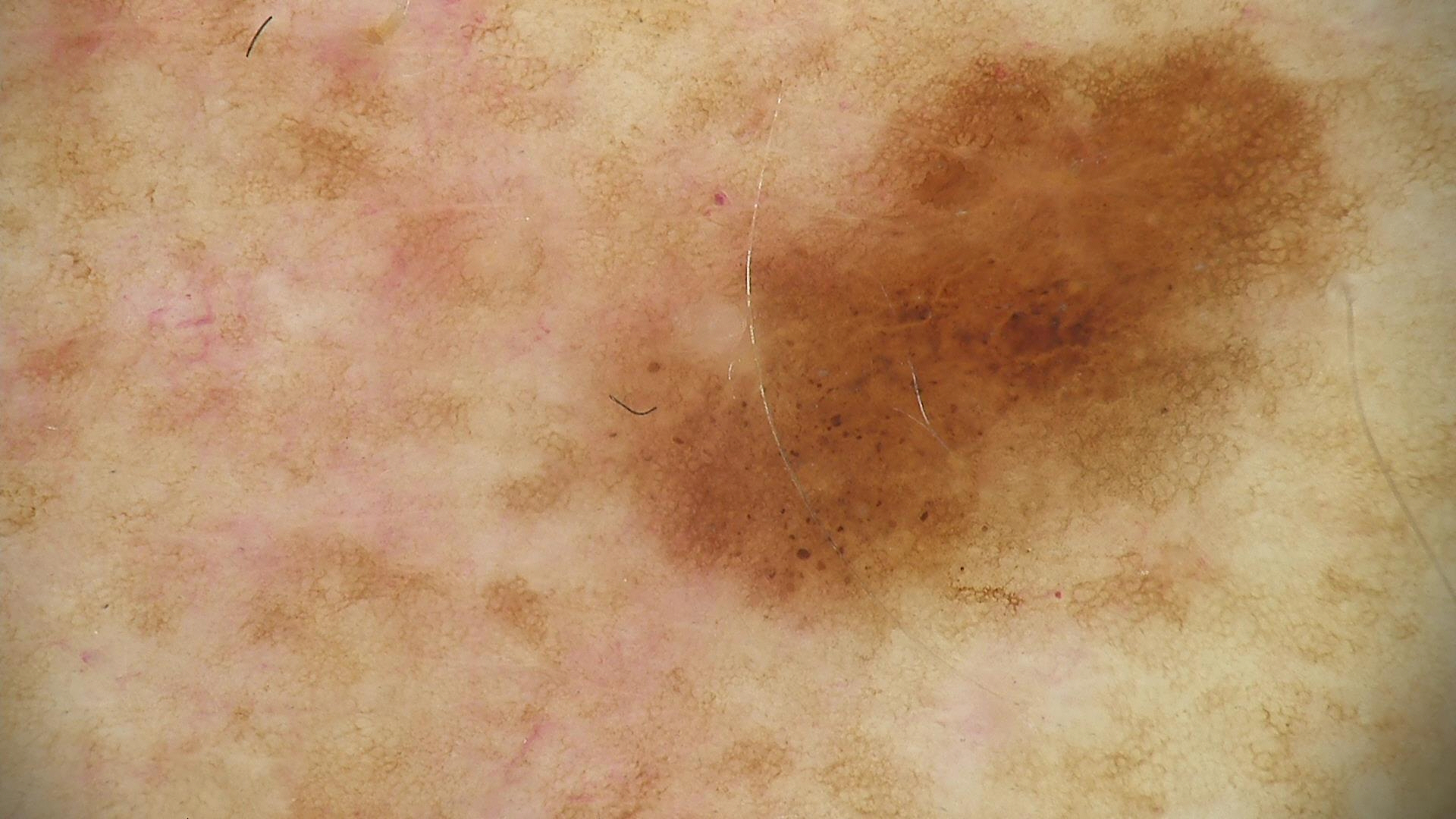A dermoscopic image of a skin lesion. The diagnosis was a dysplastic junctional nevus.